A female subject age 47. The patient says their skin tans without first burning. A moderate number of moles by the patient's own estimate. A clinical close-up of a skin lesion. The patient reports a history of sunbed use:
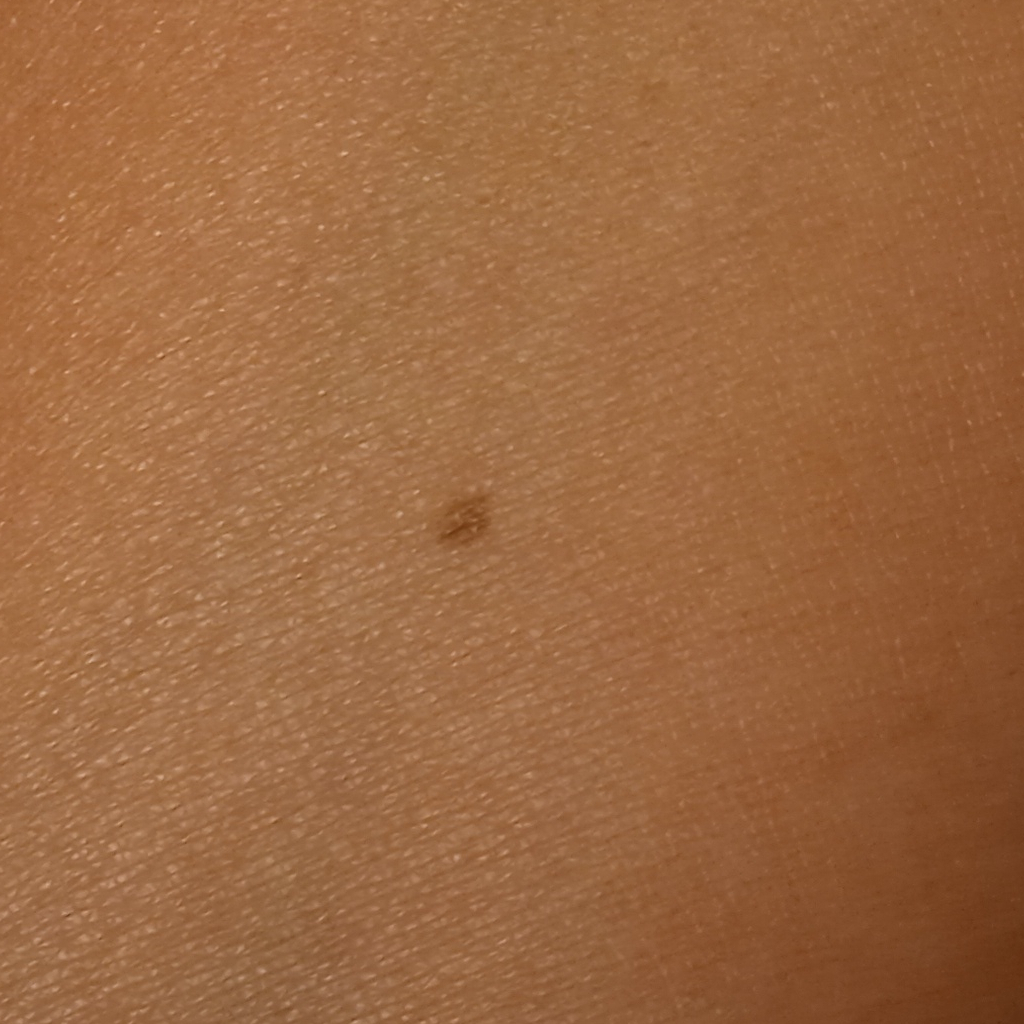site: an arm
size: 2.7 mm
diagnostic label: melanocytic nevus (dermatologist consensus)